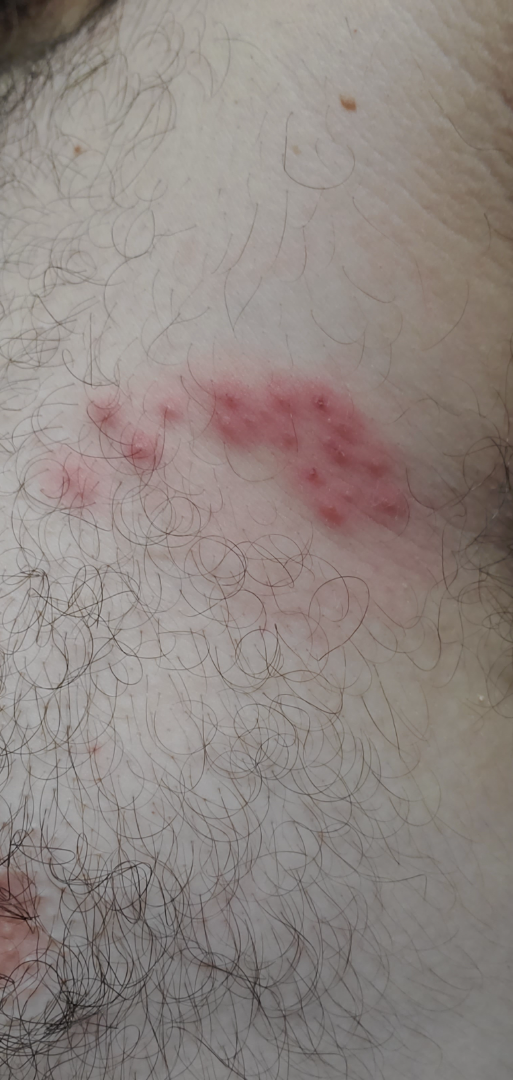assessment: most consistent with Herpes Zoster.